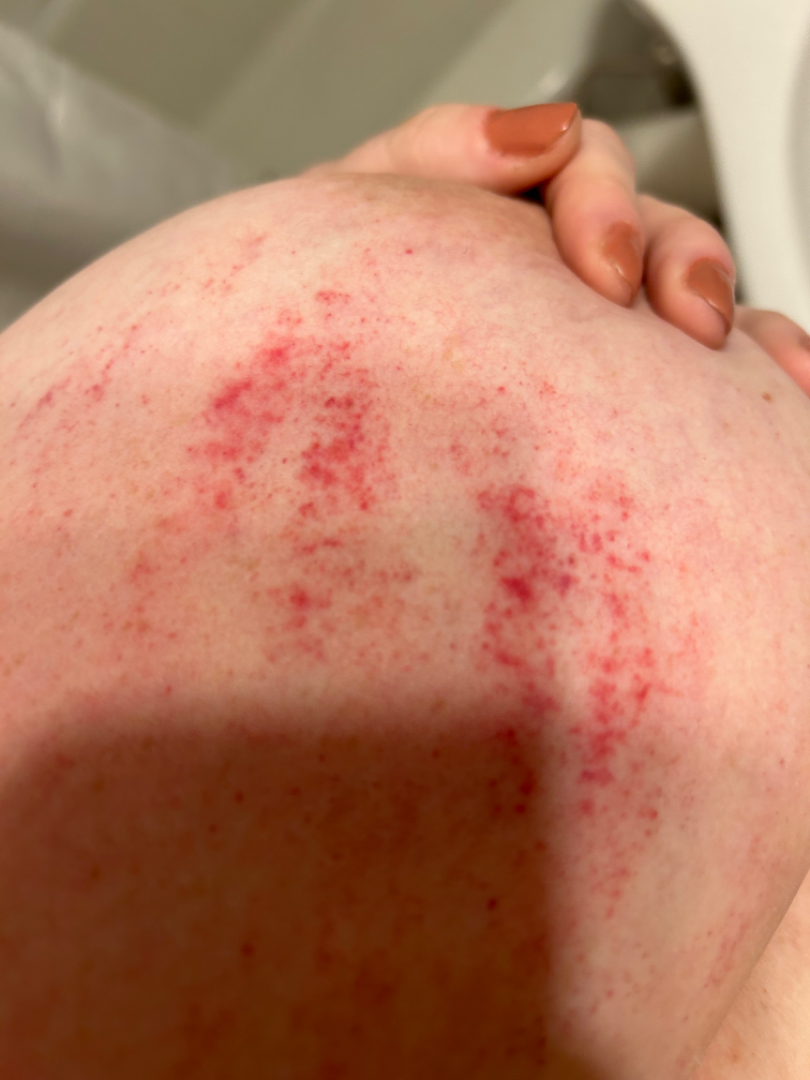Background: FST II. This is a close-up image. Findings: Consistent with ecchymoses.